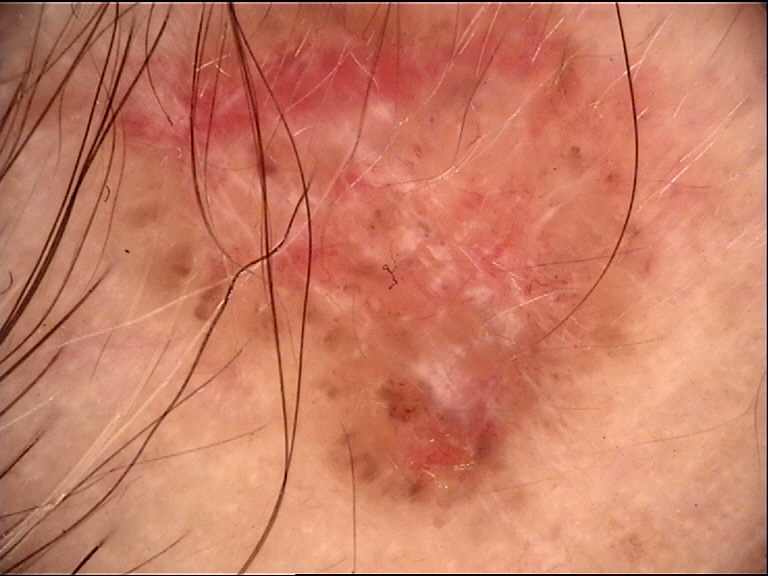A dermoscopic image of a skin lesion. This is a keratinocytic lesion. Histopathology confirmed a basal cell carcinoma.